The affected area is the front of the torso. The contributor notes the condition has been present for less than one week. A close-up photograph. Self-categorized by the patient as a rash. The lesion is described as fluid-filled. The subject is male: 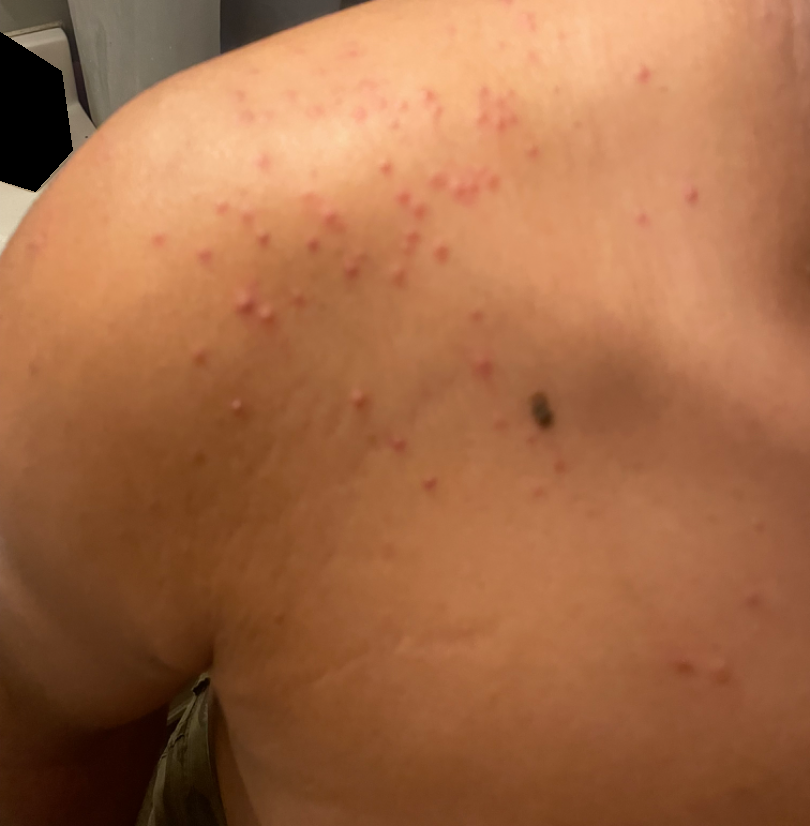assessment = not assessable.